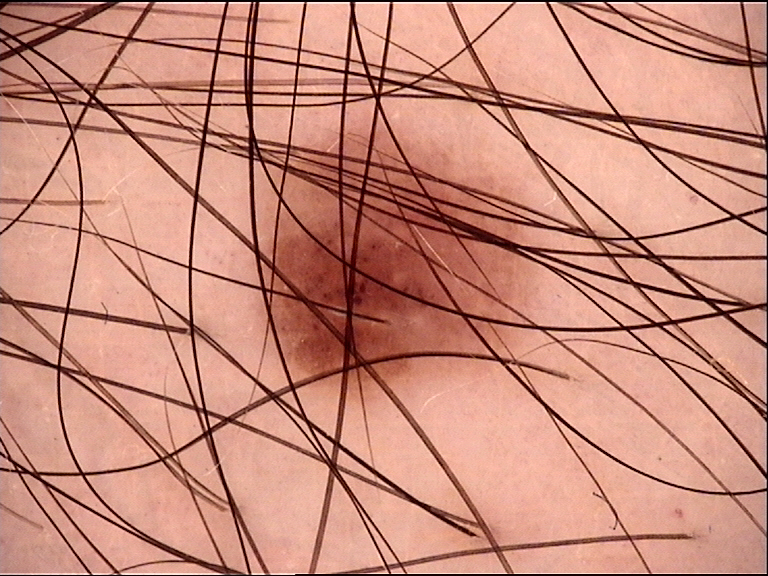image = dermoscopy, diagnosis = dysplastic junctional nevus (expert consensus).